Female contributor, age 30–39. The leg is involved. The photograph was taken at an angle:
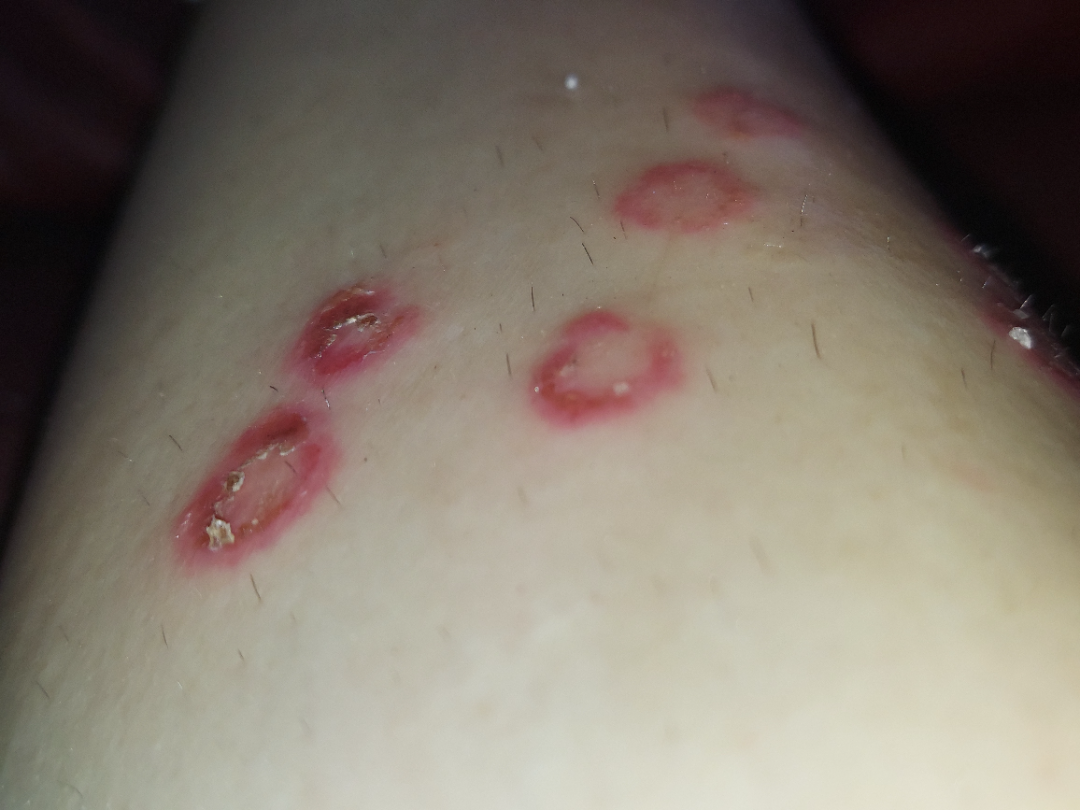| field | value |
|---|---|
| assessment | not assessable |
| systemic symptoms | none reported |
| onset | less than one week |
| patient describes the issue as | a rash |